The subject is a male aged around 35. Dermoscopy of a skin lesion:
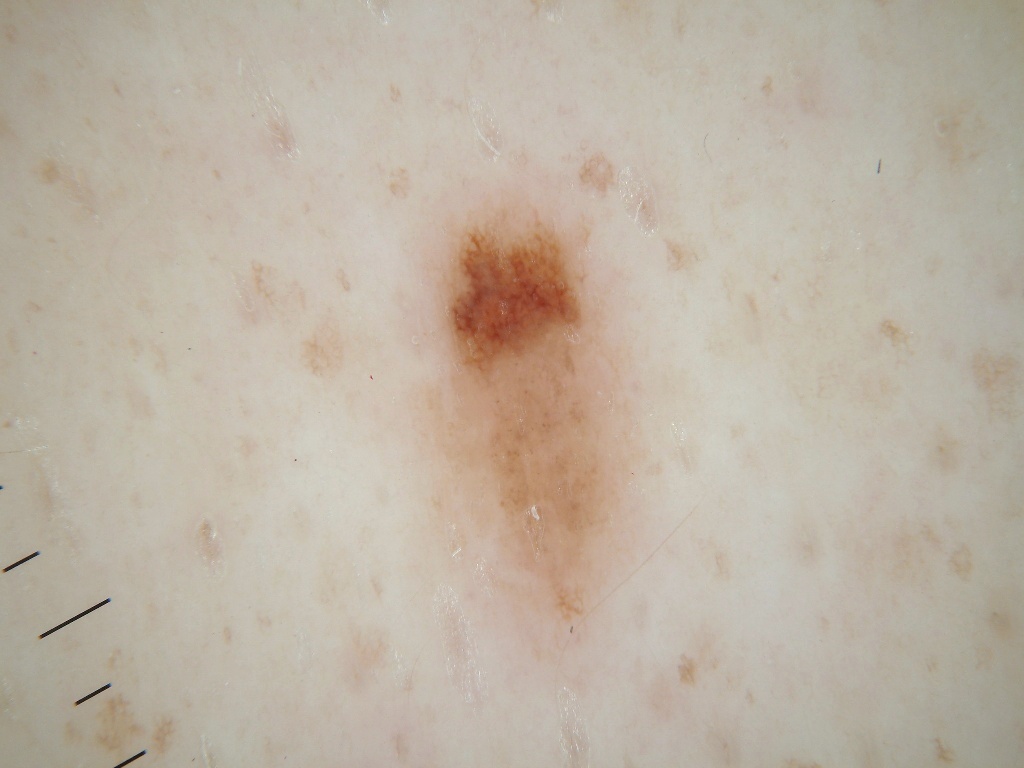In (x1, y1, x2, y2) order, the lesion's extent is 412, 163, 654, 696.
On dermoscopy, the lesion shows pigment network.
Expert review diagnosed this as a melanocytic nevus.